The back of the hand is involved · an image taken at a distance: 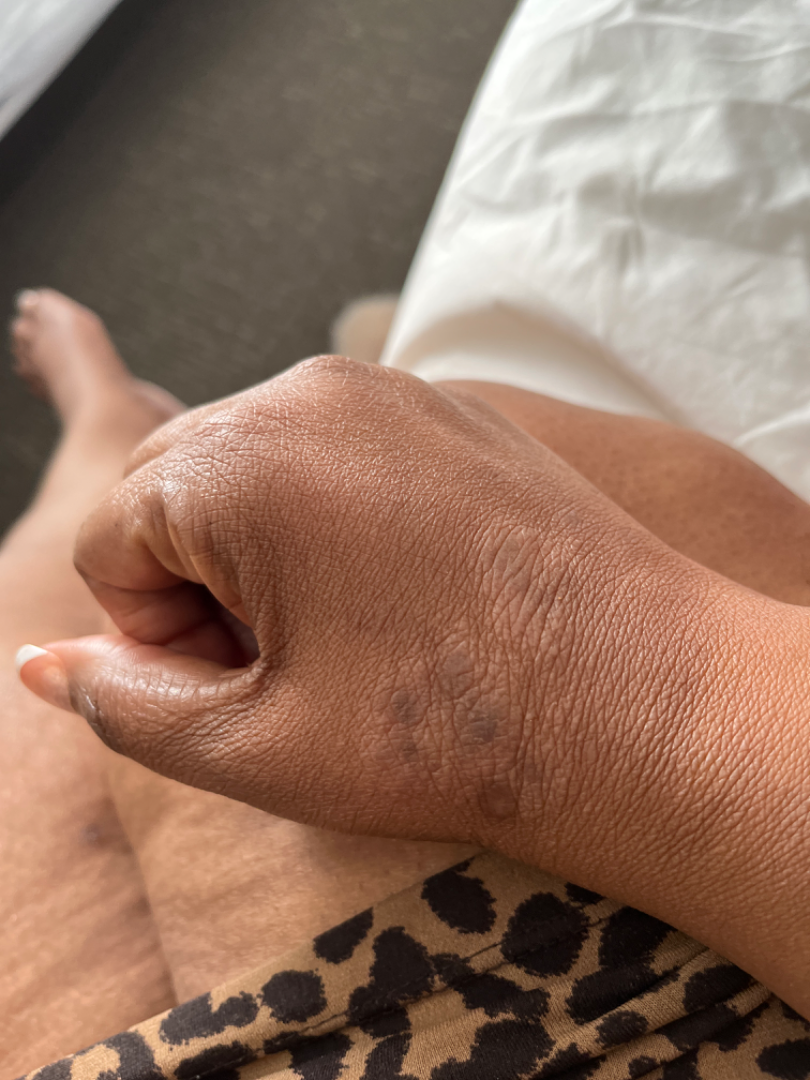{
  "texture": "raised or bumpy",
  "systemic_symptoms": "none reported",
  "patient_category": "a rash",
  "differential": {
    "leading": [
      "Lichen Simplex Chronicus"
    ],
    "considered": [
      "Cutaneous sarcoidosis"
    ],
    "unlikely": [
      "Tinea"
    ]
  }
}